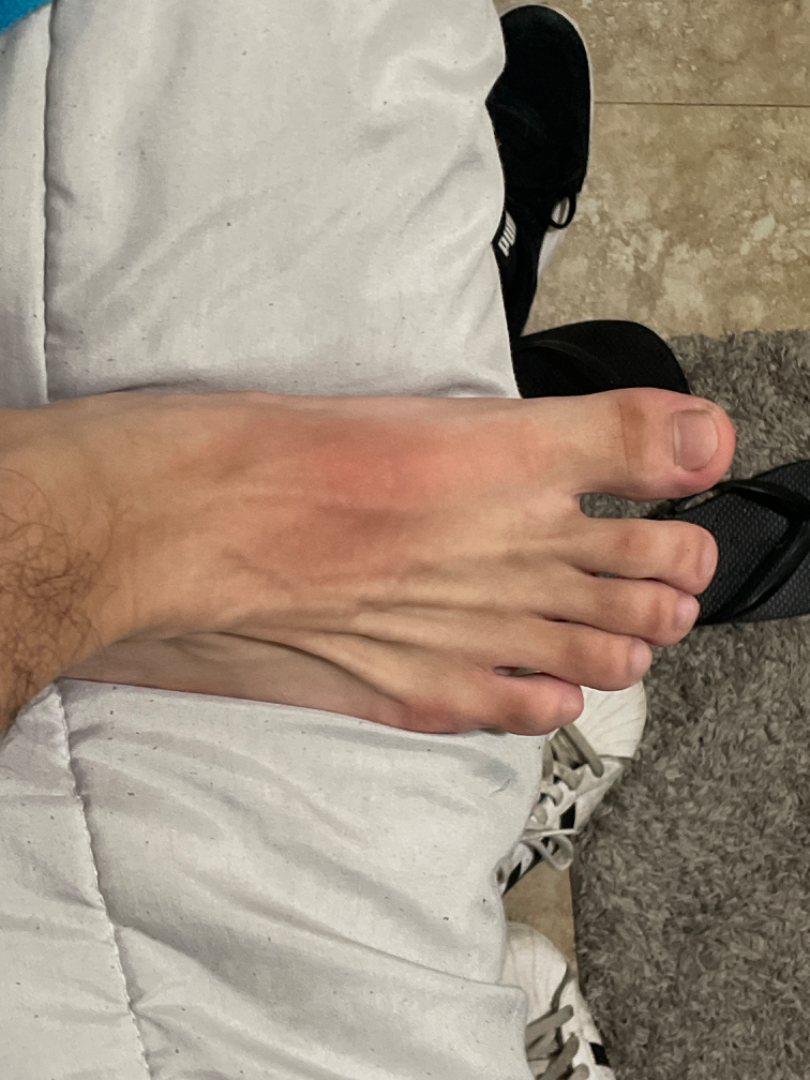The skin findings could not be characterized from the image. This image was taken at a distance.